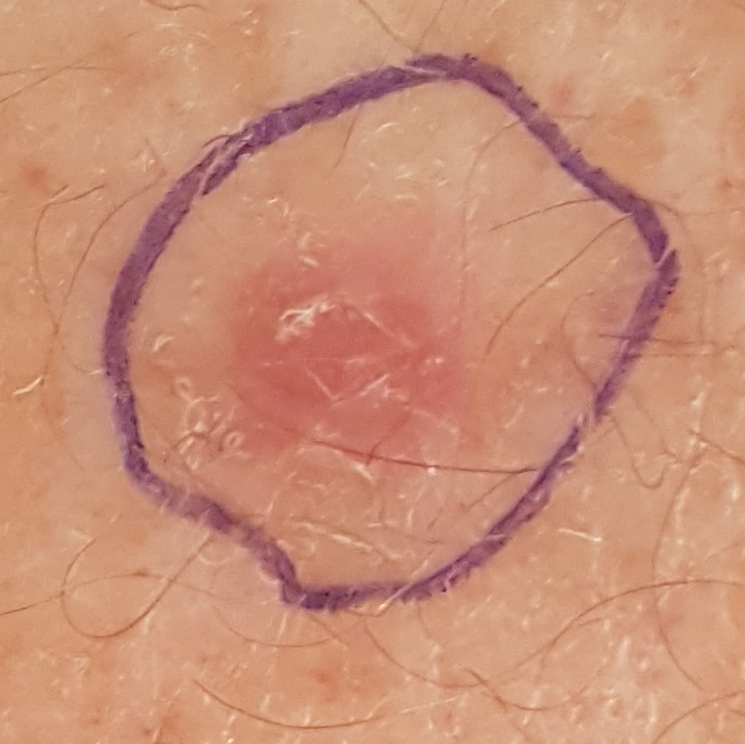• Fitzpatrick: II
• image: clinical photograph
• exposure history: alcohol use, no prior malignancy (patient or family)
• patient: male, in their 30s
• lesion size: 6 × 5 mm
• reported symptoms: no itching
• pathology: basal cell carcinoma (biopsy-proven)